Fitzpatrick skin type III · per the chart, a previous melanoma · a female patient roughly 85 years of age or older:
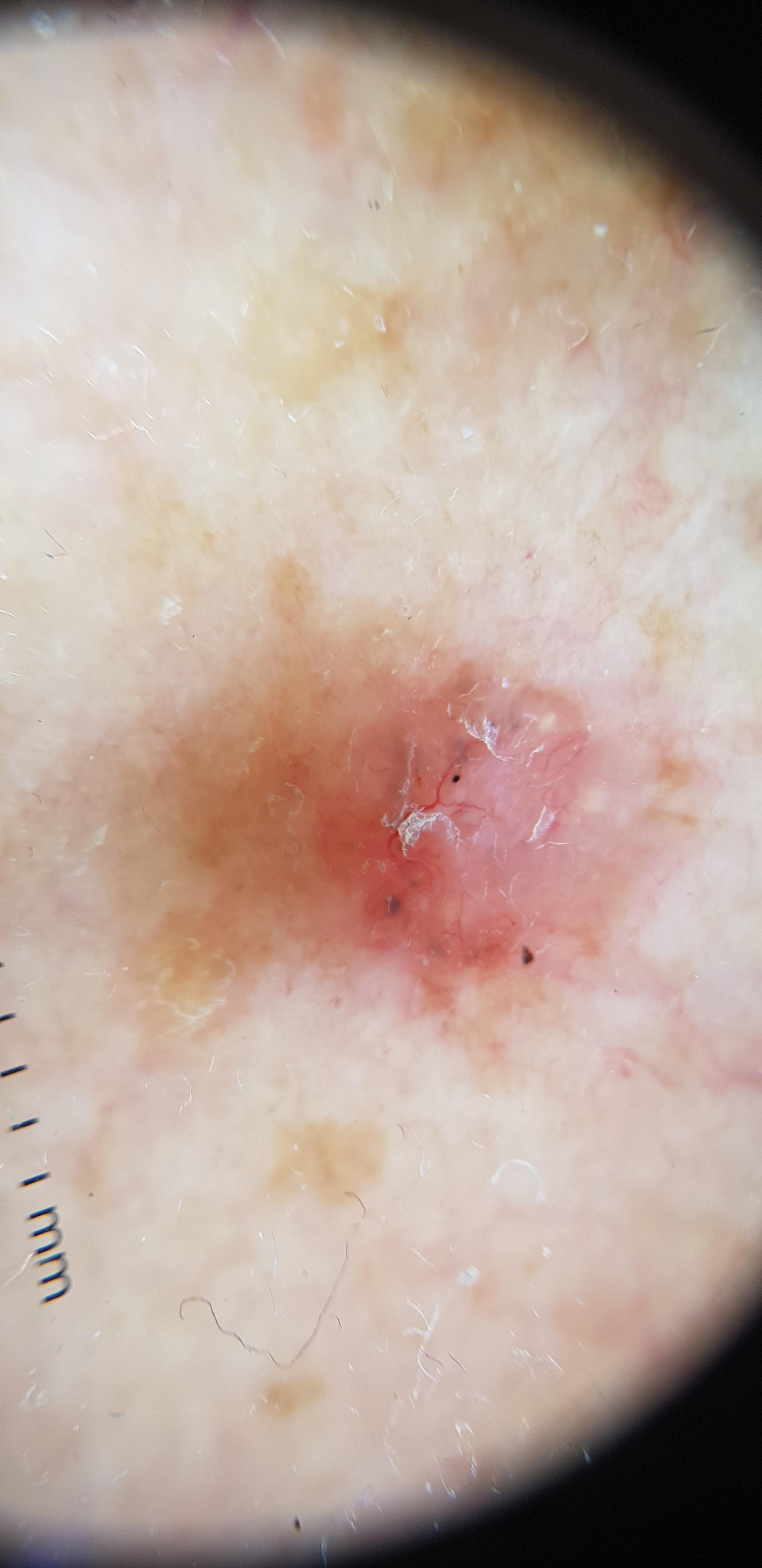{
  "lesion_location": {
    "region": "an upper extremity"
  },
  "diagnosis": {
    "name": "Basal cell carcinoma",
    "malignancy": "malignant",
    "confirmation": "histopathology",
    "lineage": "adnexal"
  }
}